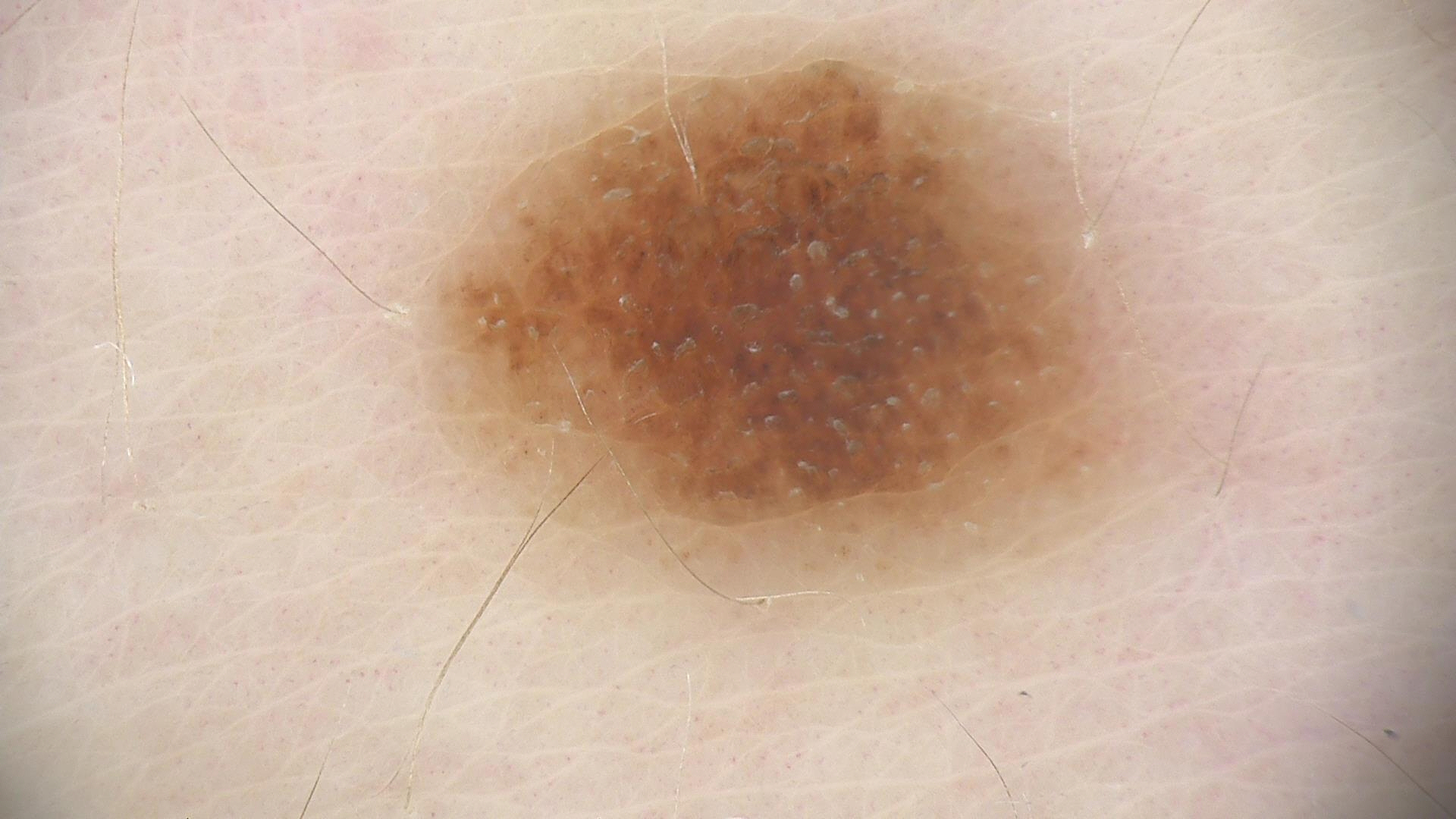imaging = dermatoscopy
assessment = compound nevus (expert consensus)